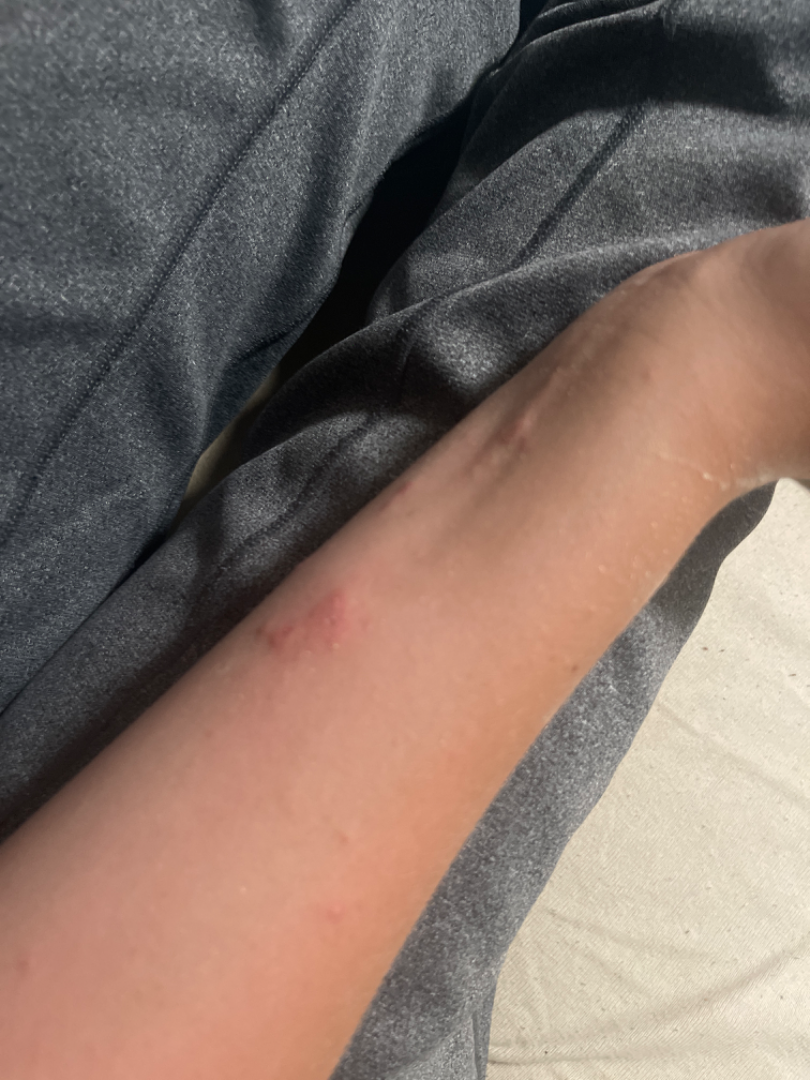patient: female
texture: raised or bumpy
shot_type: at an angle
body_site:
  - palm
  - head or neck
  - arm
skin_tone:
  fitzpatrick: II
  monk_skin_tone: 2
patient_category: a rash
symptoms: itching
differential:
  leading:
    - Allergic Contact Dermatitis
  unlikely:
    - Scabies
    - Acute dermatitis, NOS
    - Insect Bite